A male subject, in their 60s · this is a dermoscopic photograph of a skin lesion:
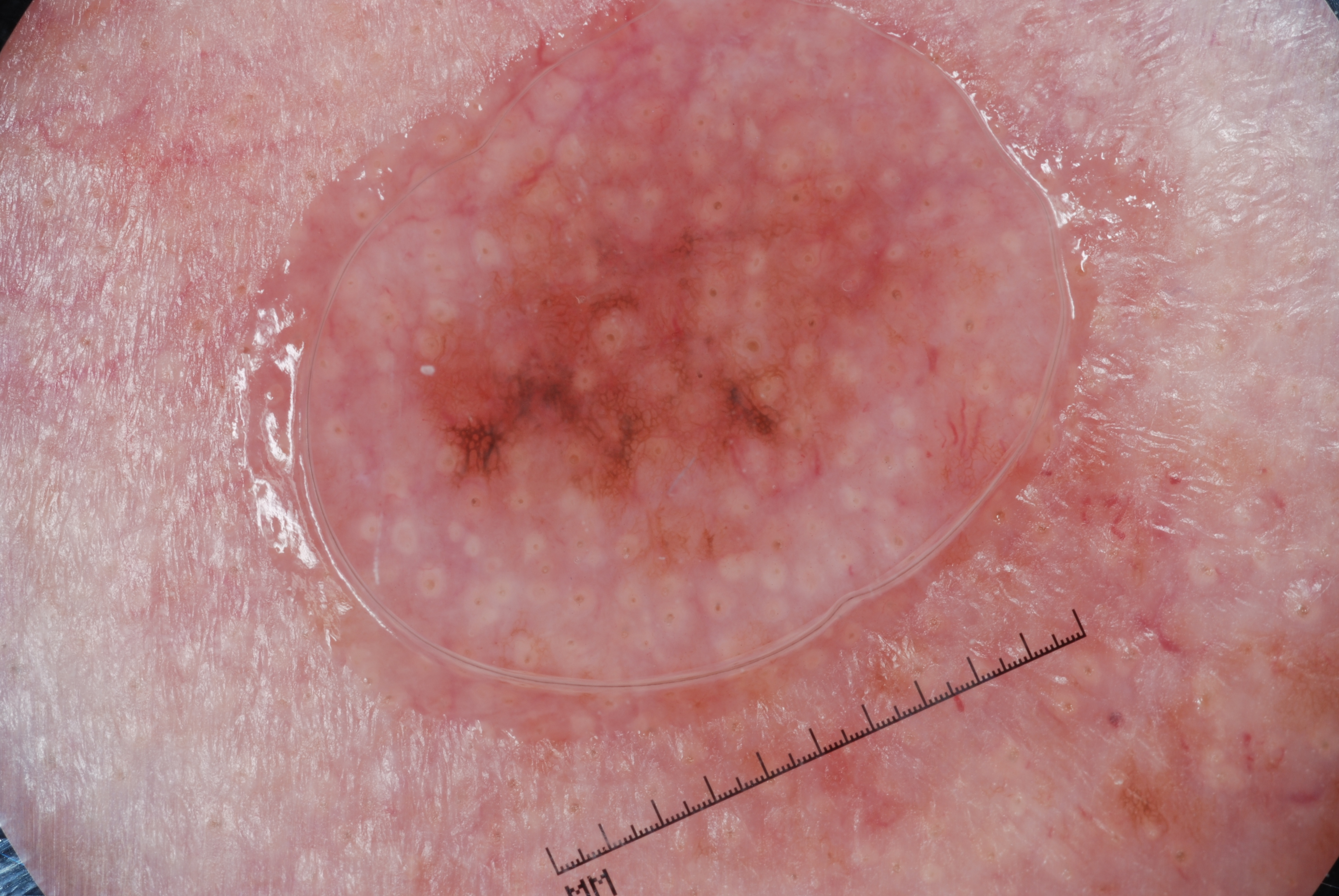features: pigment network; lesion bbox: [406, 105, 936, 573]; lesion size: moderate; impression: a melanoma.